A dermoscopic photograph of a skin lesion.
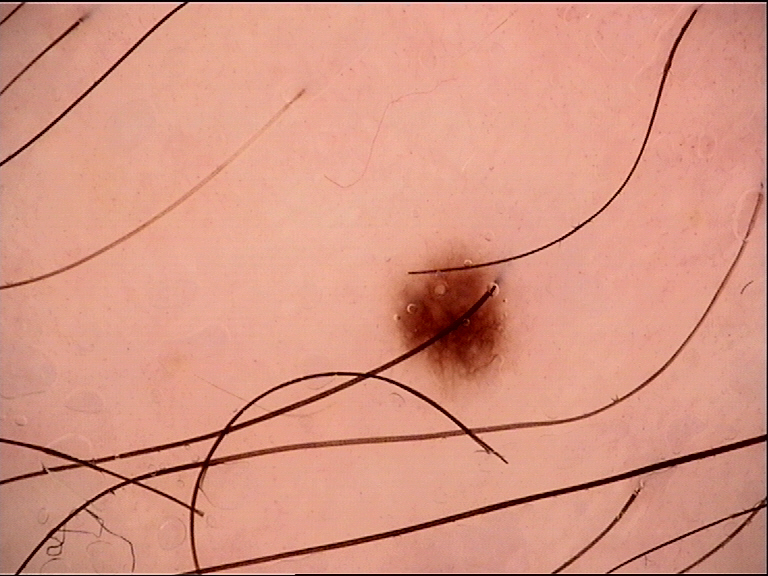The diagnosis was a benign lesion — a dysplastic junctional nevus.